This image was taken at a distance, skin tone: lay graders estimated MST 2 or 3:
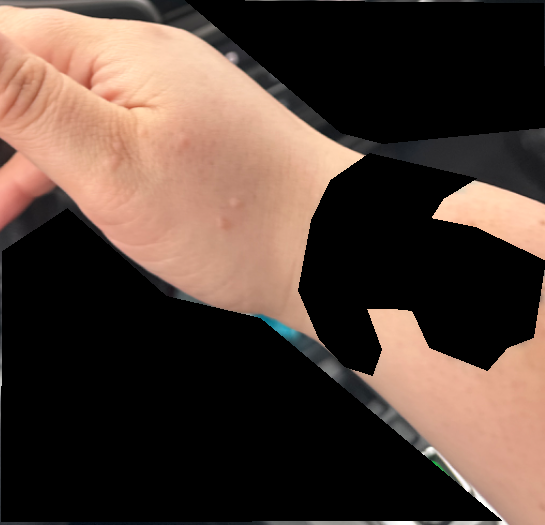Q: What was the assessment?
A: indeterminate